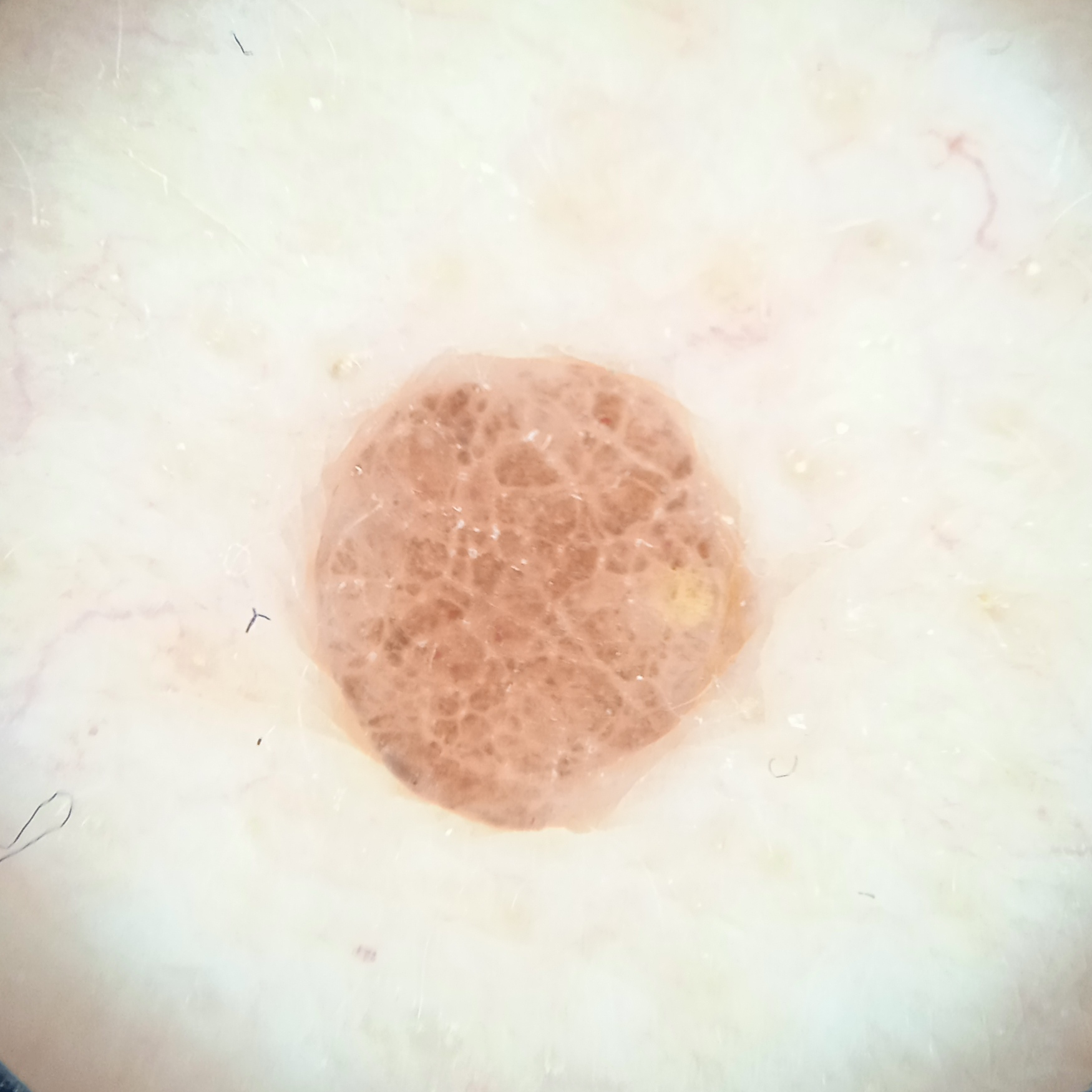A dermatoscopic image of a skin lesion. The patient says their skin reddens painfully with sun exposure. The patient reports a family history of skin cancer, a personal history of skin cancer, and immunosuppression. Imaged for a research study, with no referral diagnosis recorded. Numerous moles by the patient's own estimate. The lesion involves an arm. The lesion is about 3 mm across. The consensus diagnosis for this lesion was a melanocytic nevus.